Close-up view. The affected area is the head or neck and arm. The subject is 18–29, female: 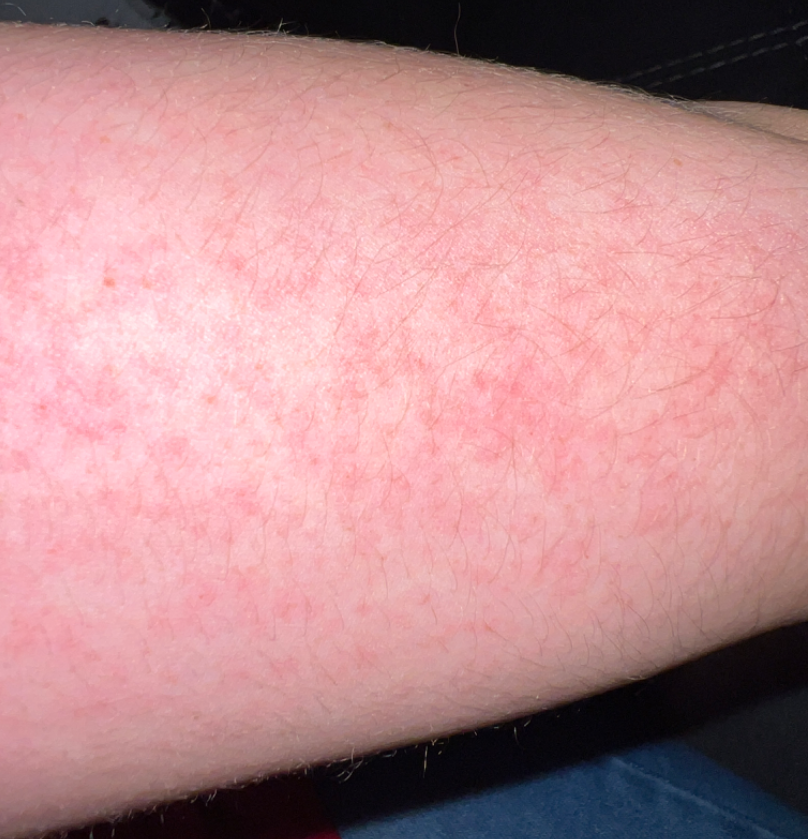Diagnostic features were not clearly distinguishable in this photograph.